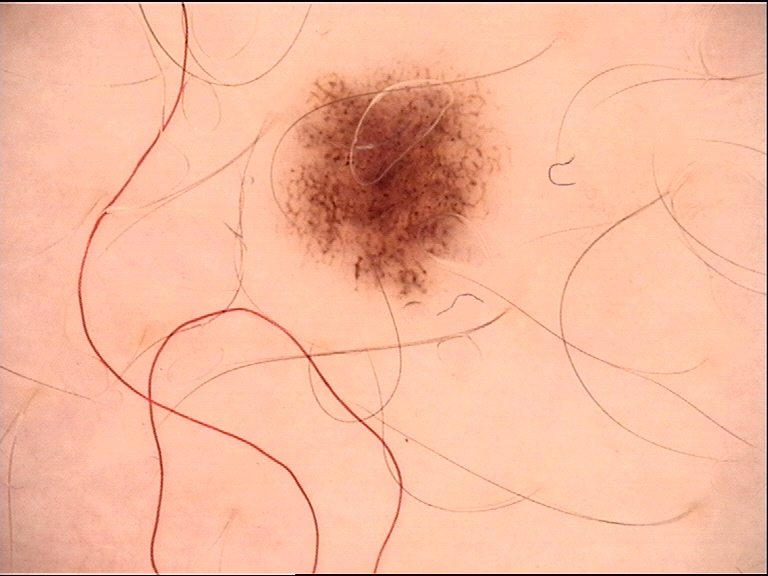A dermoscopy image of a single skin lesion. The diagnostic label was a benign lesion — a dysplastic junctional nevus.